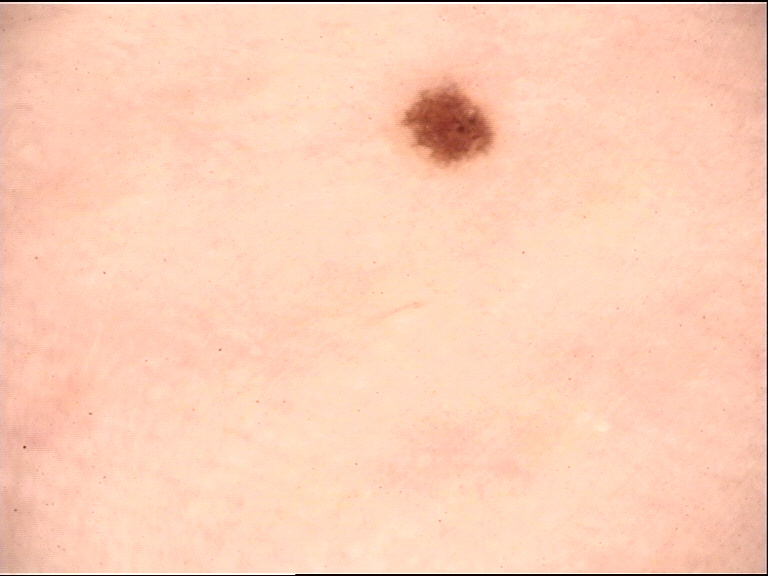<dermoscopy>
<diagnosis>
<name>dysplastic junctional nevus</name>
<code>jd</code>
<malignancy>benign</malignancy>
<super_class>melanocytic</super_class>
<confirmation>expert consensus</confirmation>
</diagnosis>
</dermoscopy>